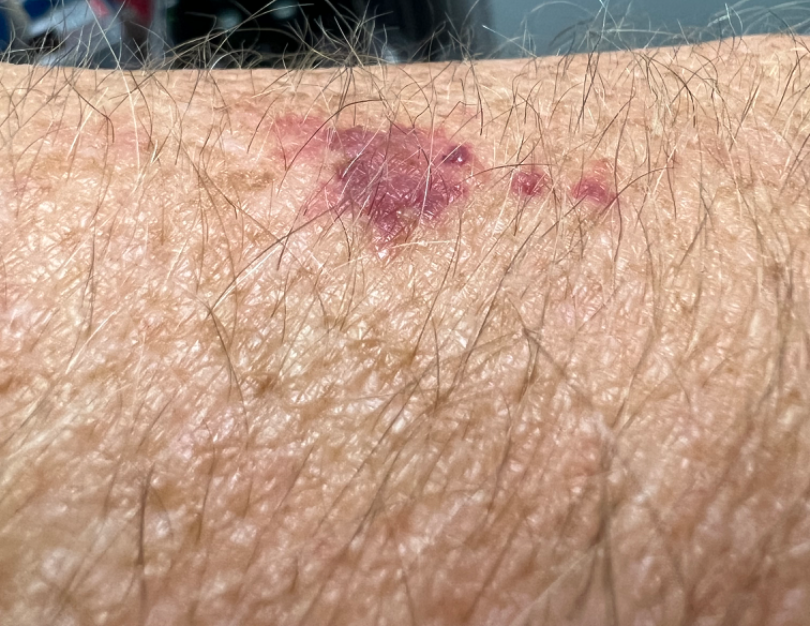{"differential": {"ecchymoses": 1.0}}